A dermoscopic close-up of a skin lesion: 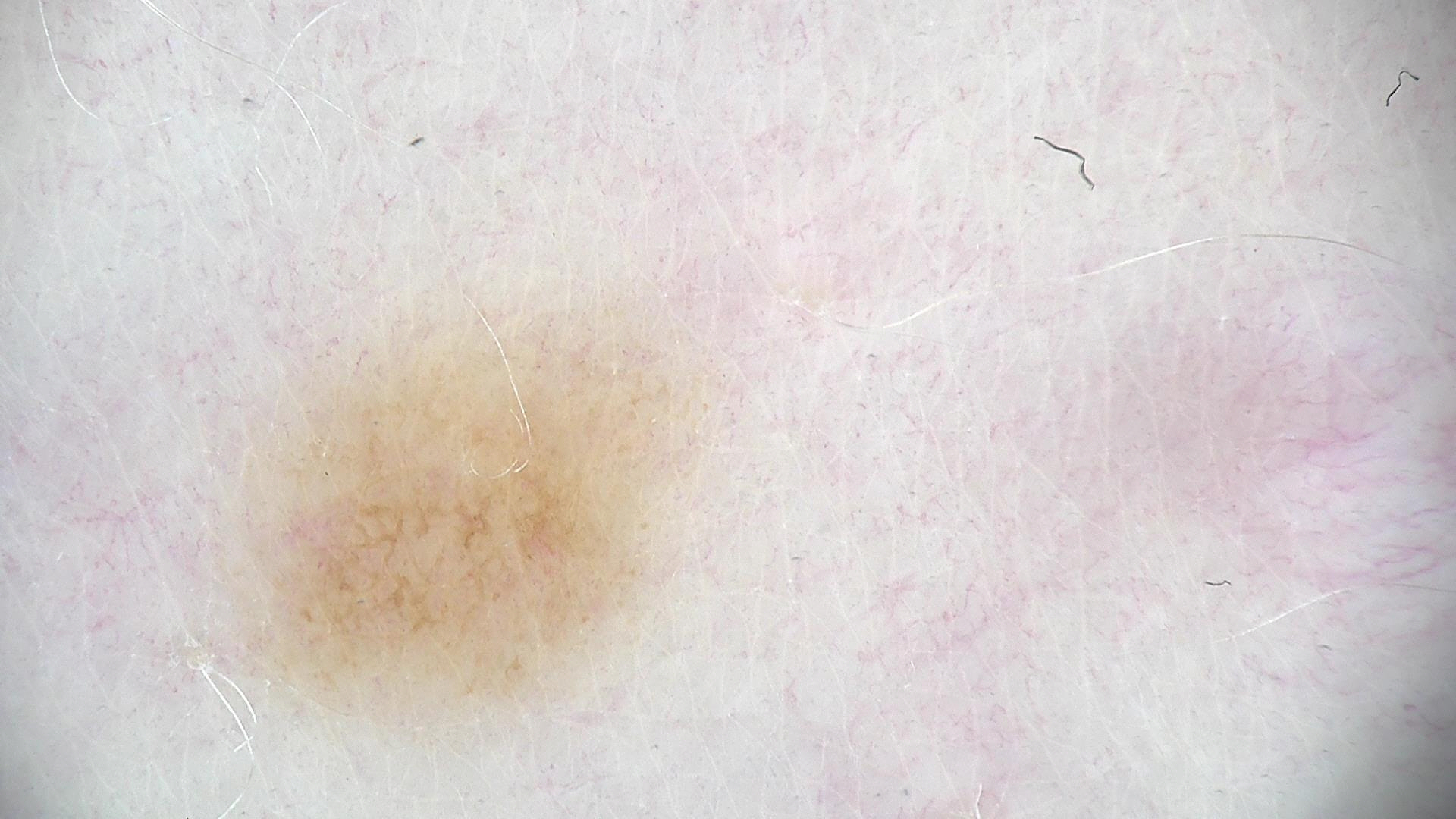The diagnosis was a dysplastic junctional nevus.